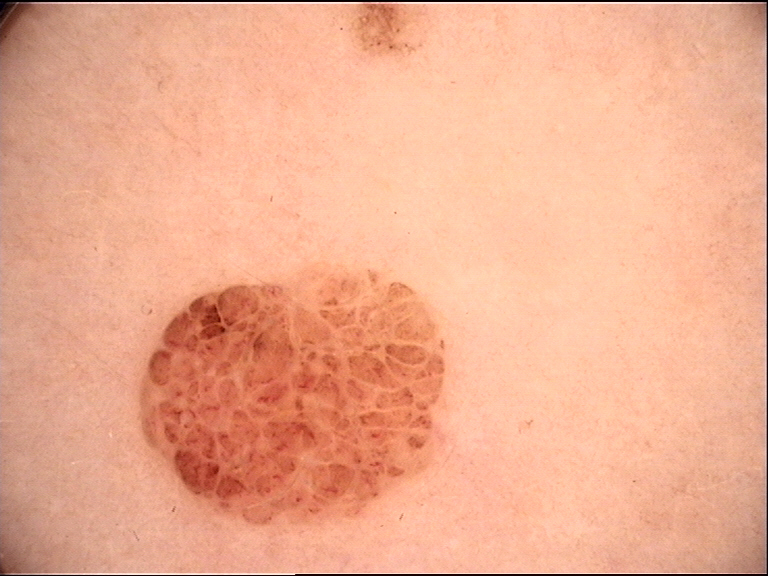• imaging · dermoscopy
• lesion type · banal
• label · compound nevus (expert consensus)